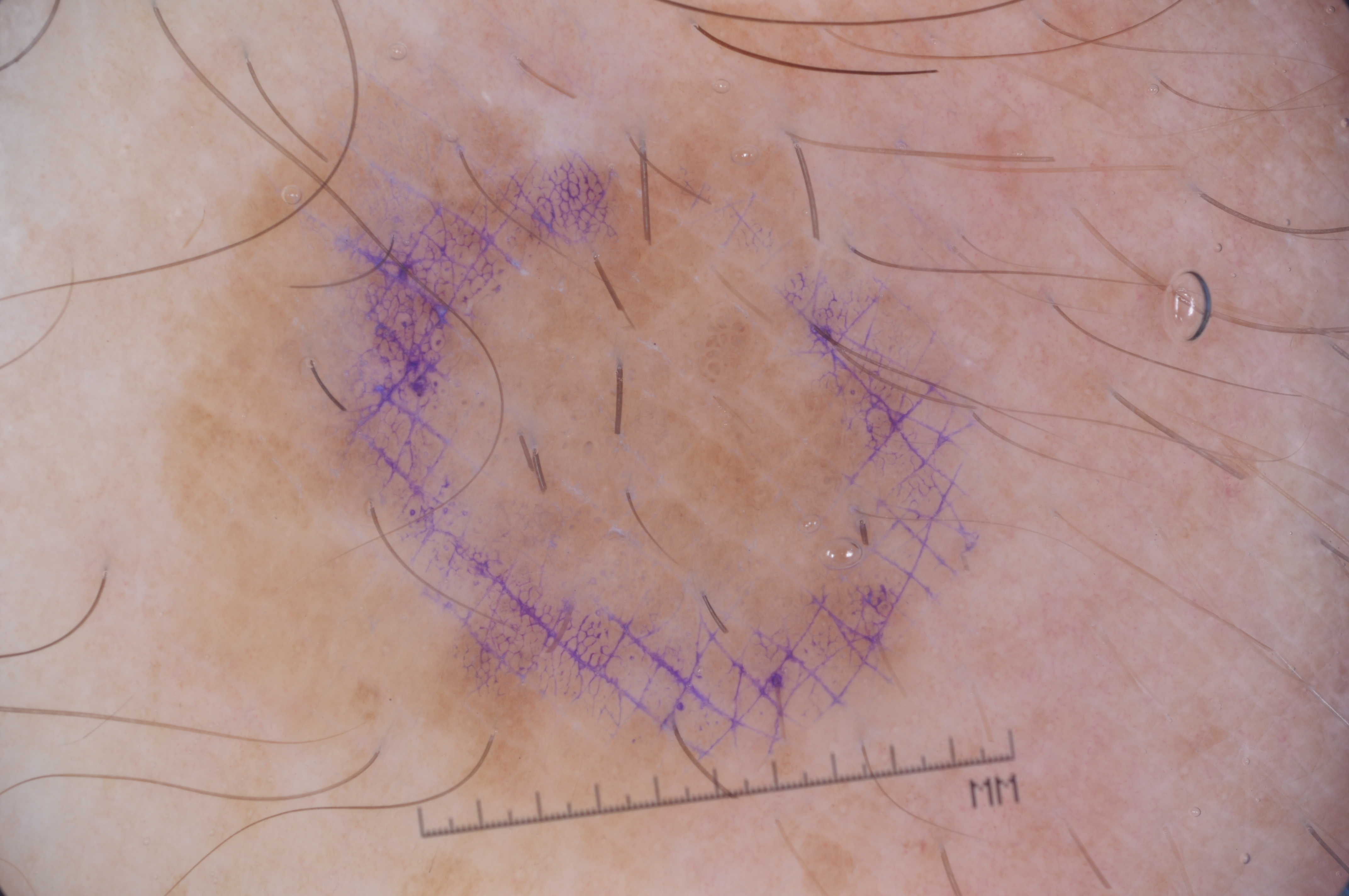| key | value |
|---|---|
| image | dermoscopy of a skin lesion |
| patient | male, aged approximately 55 |
| extent | large |
| lesion location | x1=147, y1=85, x2=1075, y2=847 |
| absent dermoscopic features | pigment network, streaks, milia-like cysts, and negative network |
| diagnosis | a seborrheic keratosis, a benign lesion |